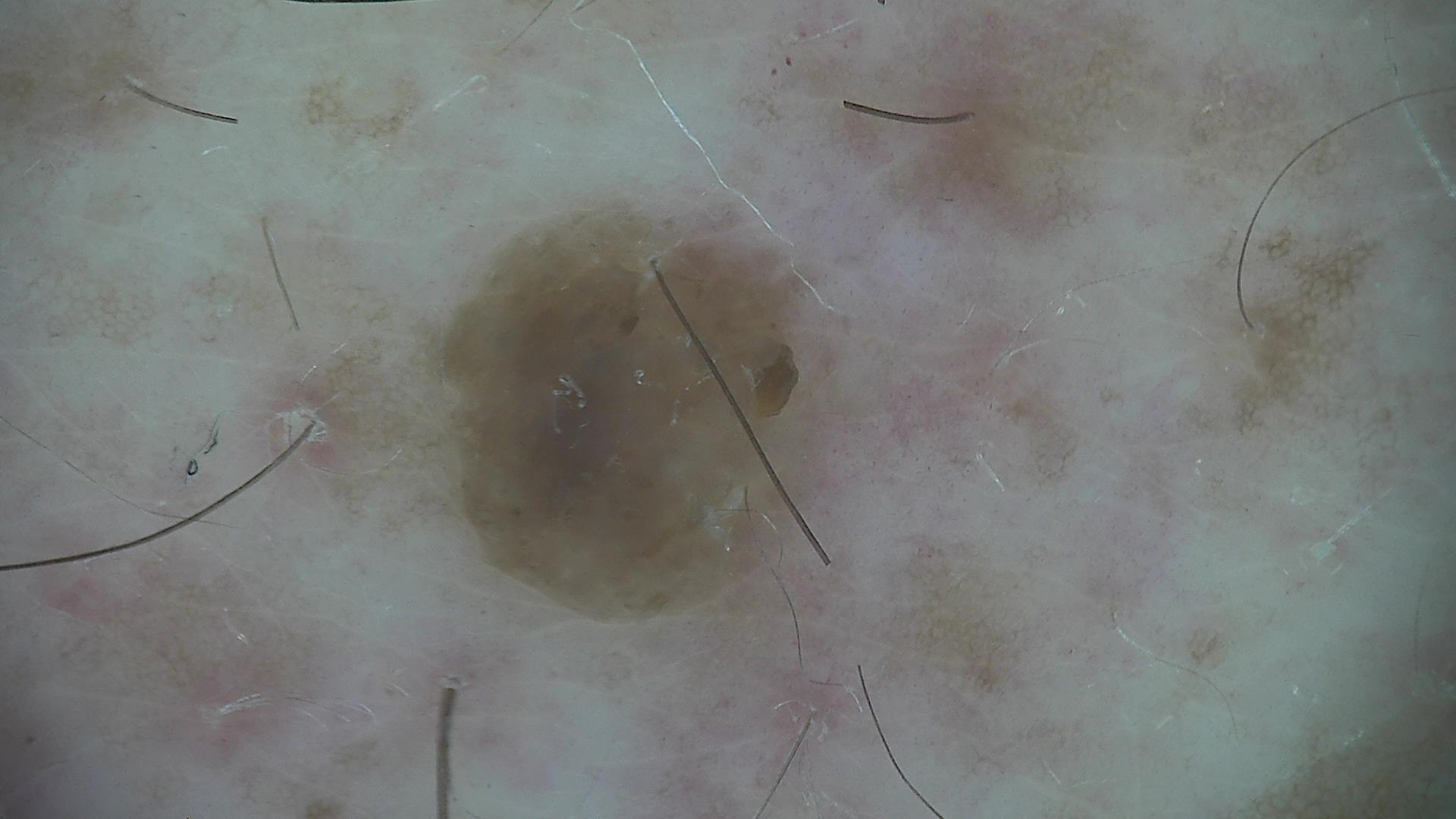Case:
* assessment — seborrheic keratosis (expert consensus)